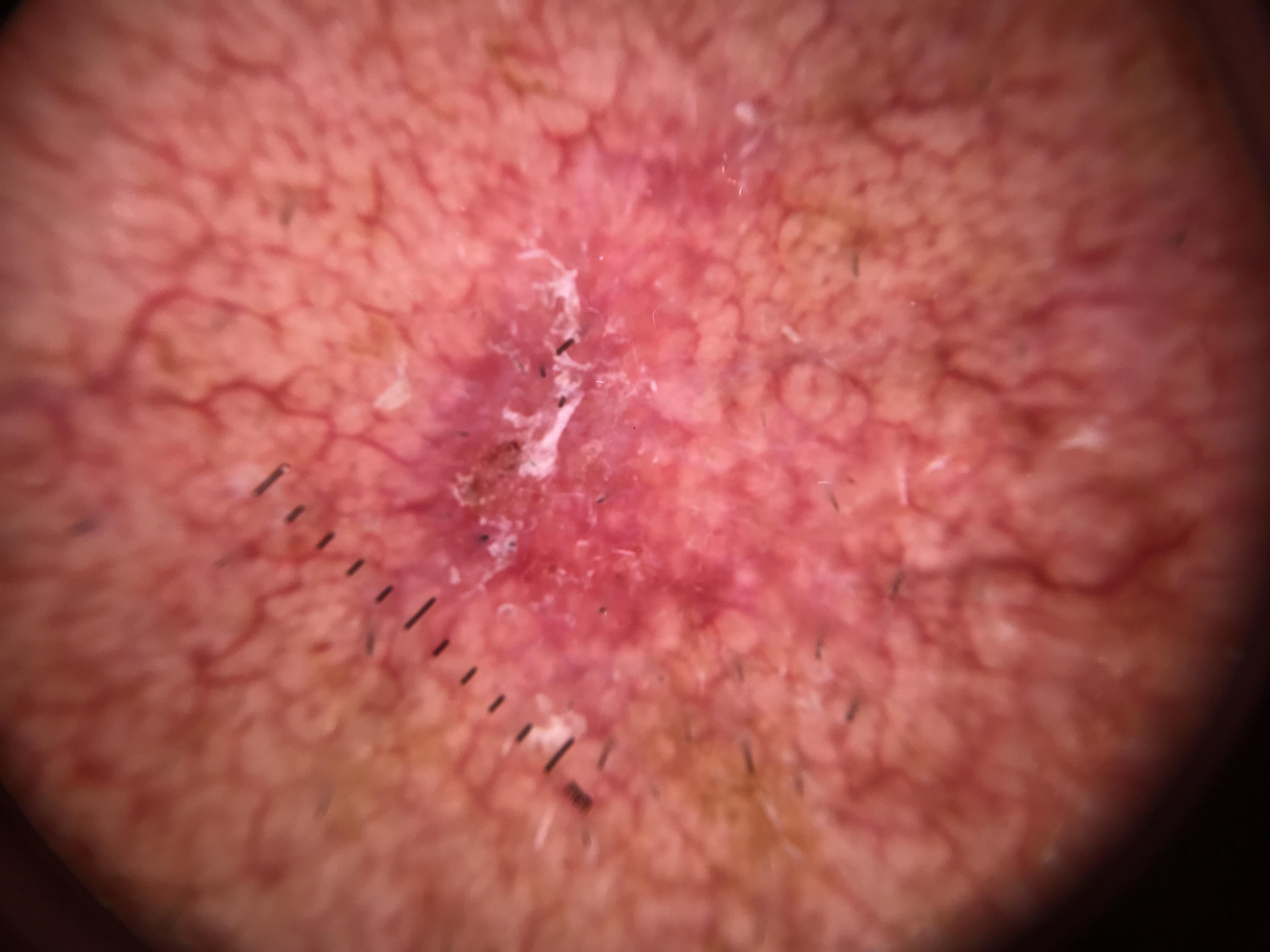Case:
* body site — the head or neck
* pathology — Basal cell carcinoma (biopsy-proven)